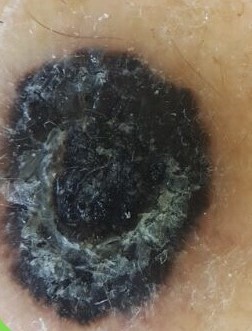Confirmed on histopathology as a melanoma.